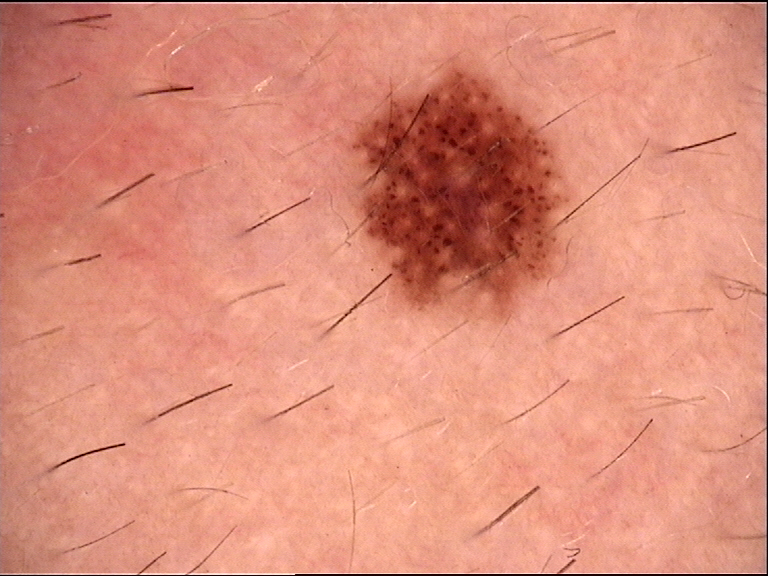| field | value |
|---|---|
| modality | dermatoscopy |
| diagnosis | dysplastic junctional nevus (expert consensus) |